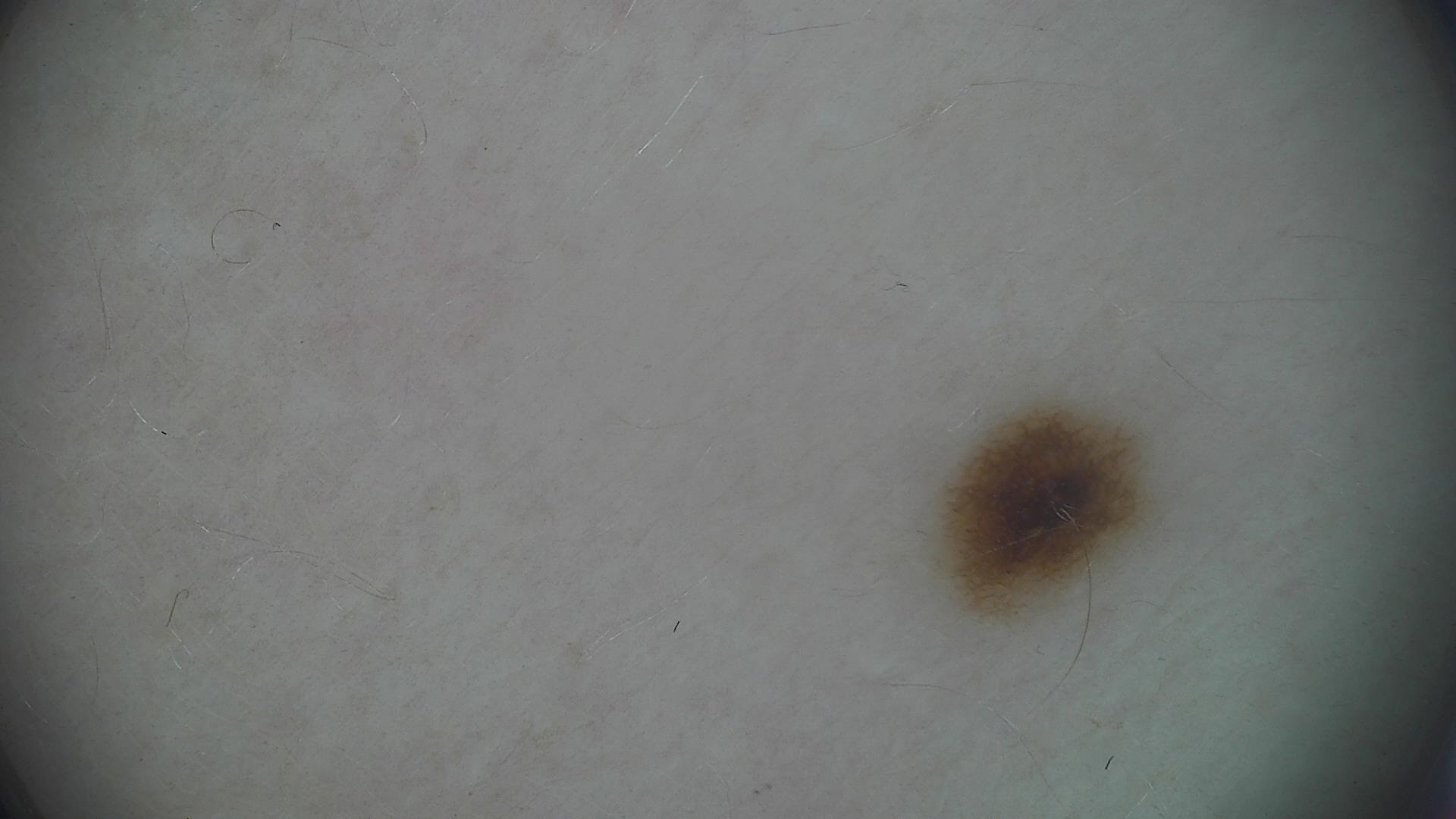  diagnosis:
    name: dysplastic junctional nevus
    code: jd
    malignancy: benign
    super_class: melanocytic
    confirmation: expert consensus